A dermoscopic image of a skin lesion.
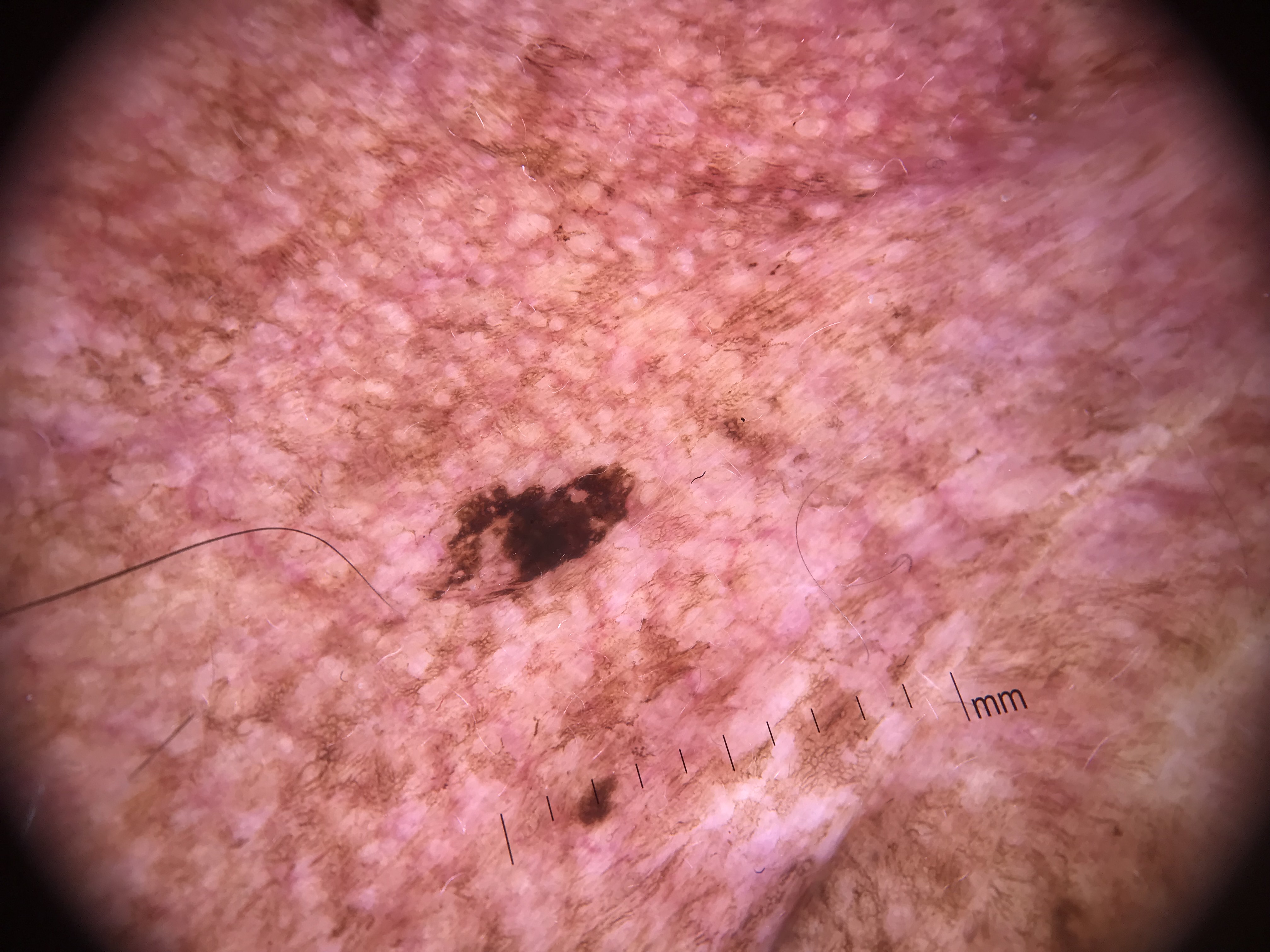The biopsy diagnosis was a lentigo maligna.